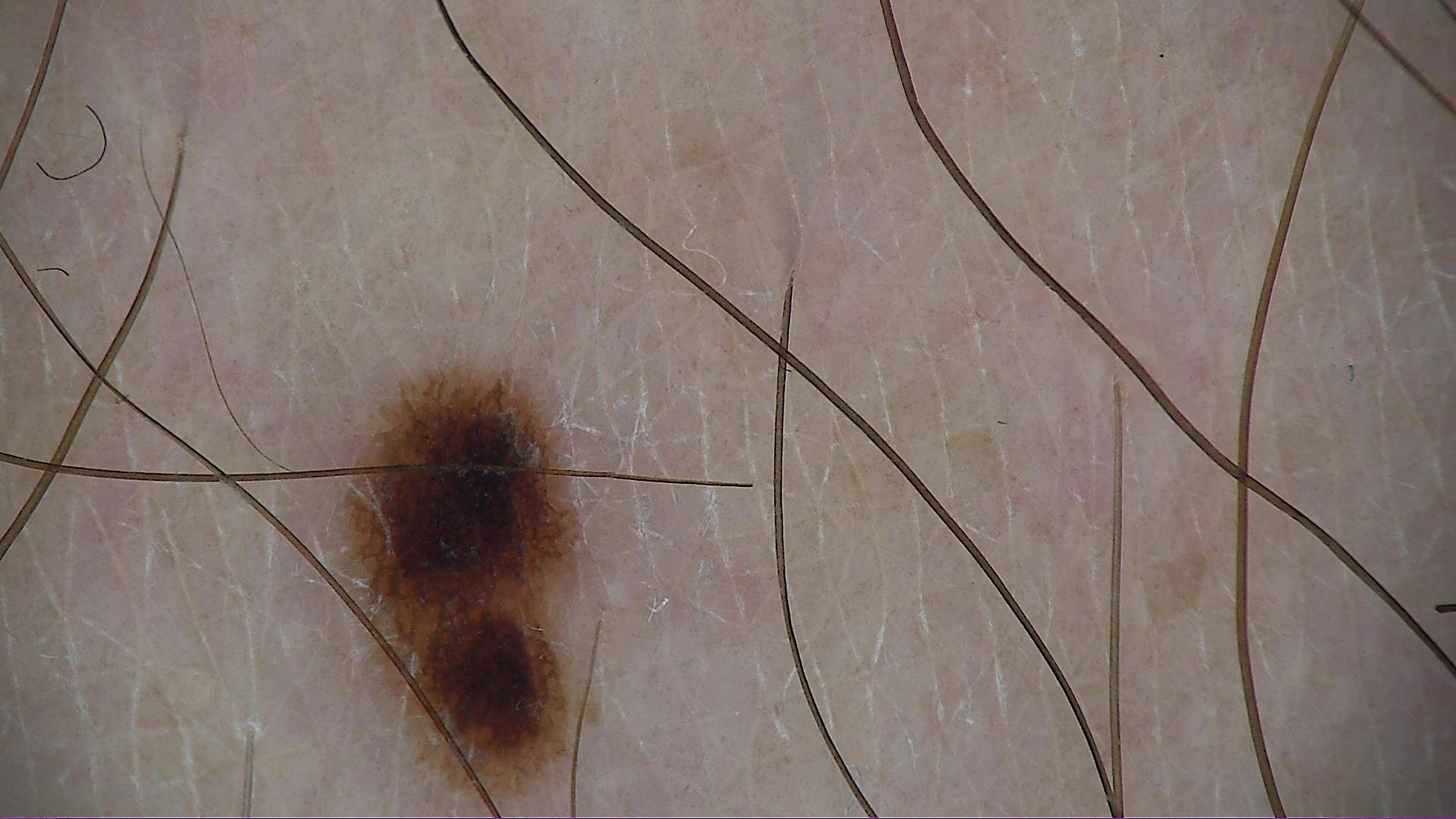A dermoscopic image of a skin lesion.
The diagnosis was a dysplastic junctional nevus.